A skin lesion imaged with a dermatoscope; a male subject age 65; the patient says their skin reddens painfully with sun exposure:
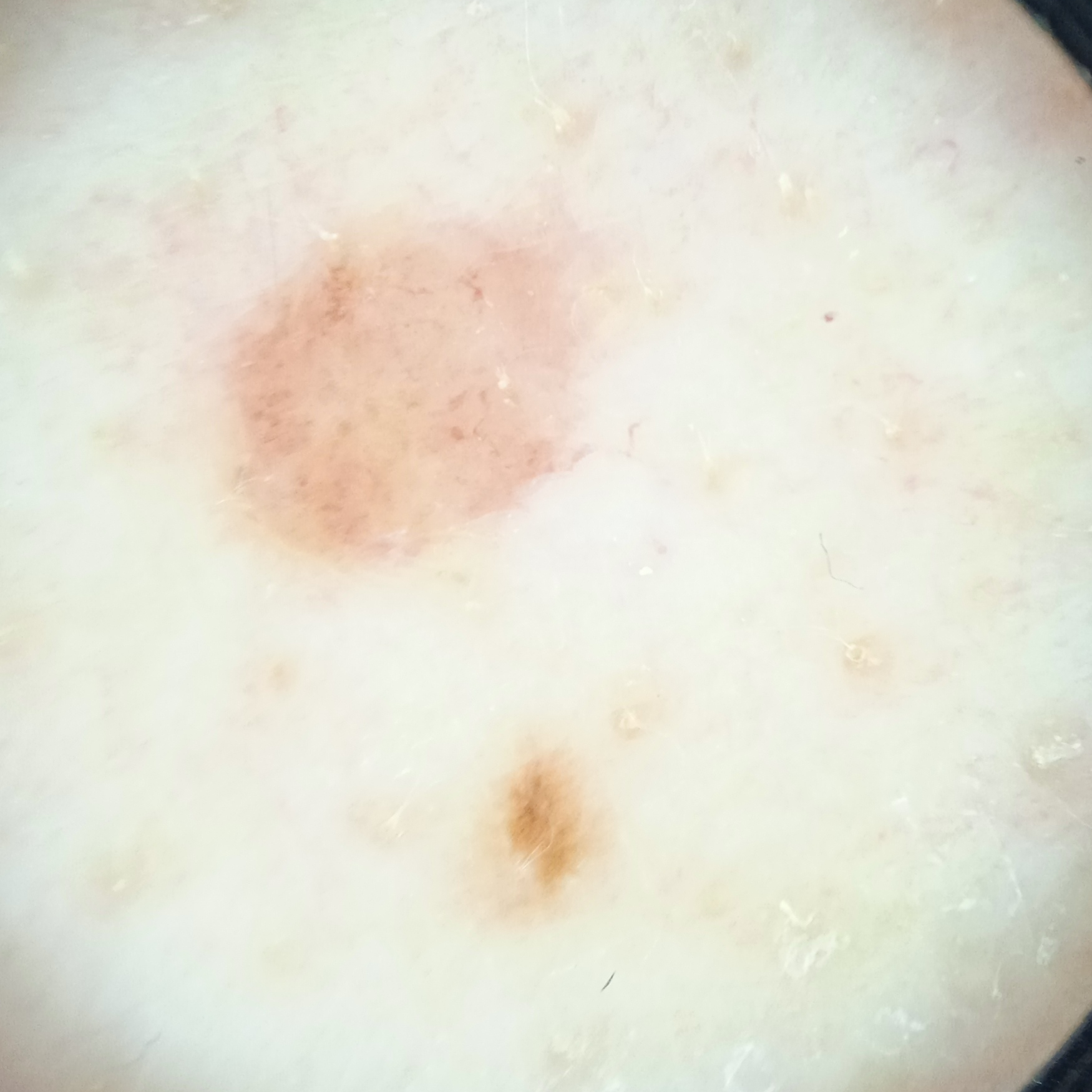Summary: Located on the back. The lesion measures approximately 4.4 mm. Assessment: The consensus diagnosis for this lesion was a melanocytic nevus.